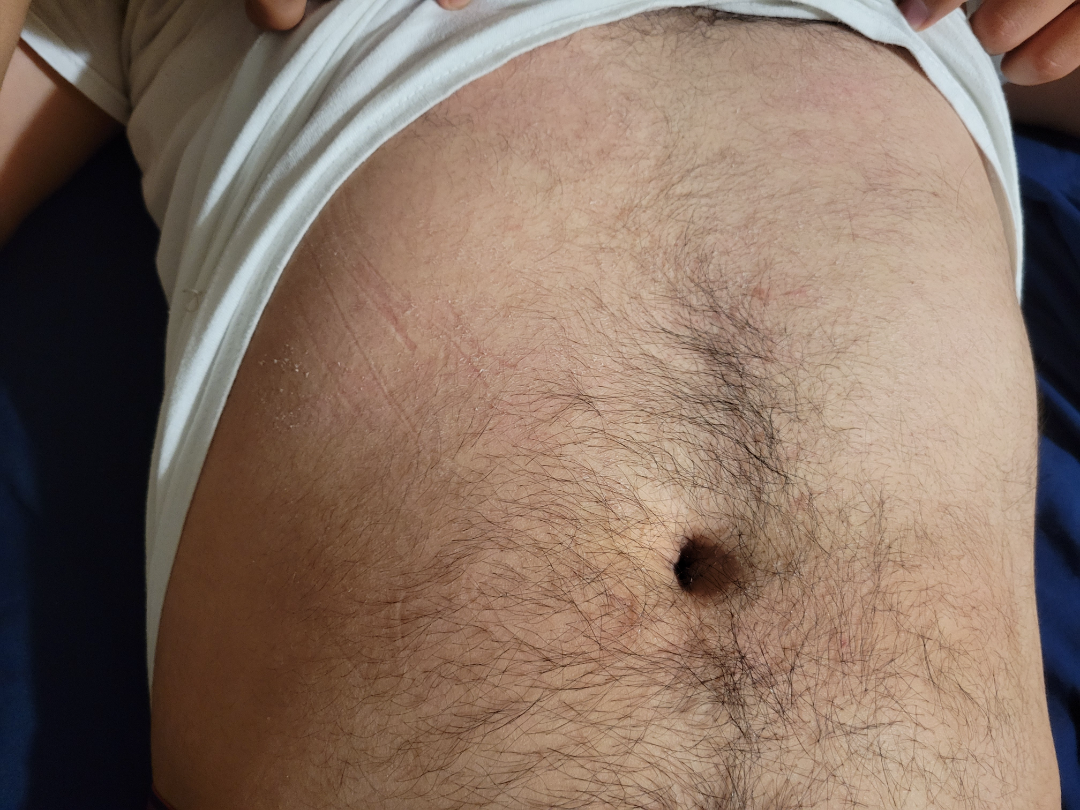Q: What is the affected area?
A: back of the torso and front of the torso
Q: Who is the patient?
A: male, age 18–29
Q: How was the photo taken?
A: at a distance
Q: What is the dermatologist's impression?
A: most likely Eczema; possibly Pityriasis lichenoides; also raised was Tinea